A clinical photograph showing a skin lesion · acquired for a research image collection, with no referral diagnosis · a female patient aged 15.
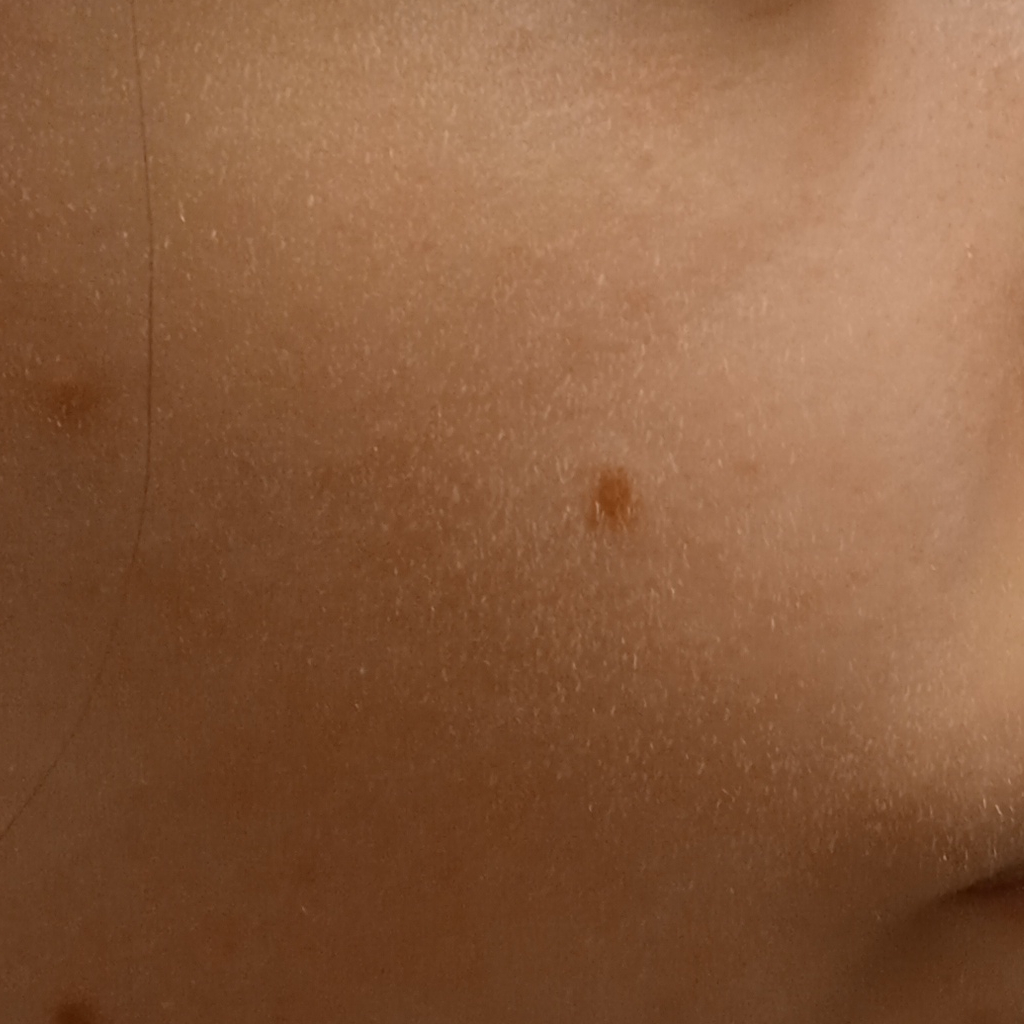Case:
– body site: the face
– lesion size: 3.2 mm
– diagnosis: melanocytic nevus (dermatologist consensus)